The patient says their skin reddens painfully with sun exposure · numerous moles by the patient's own estimate · by self-report, immunosuppression, a family history of skin cancer, a personal history of skin cancer, and no prior organ transplant · a skin lesion imaged with a dermatoscope:
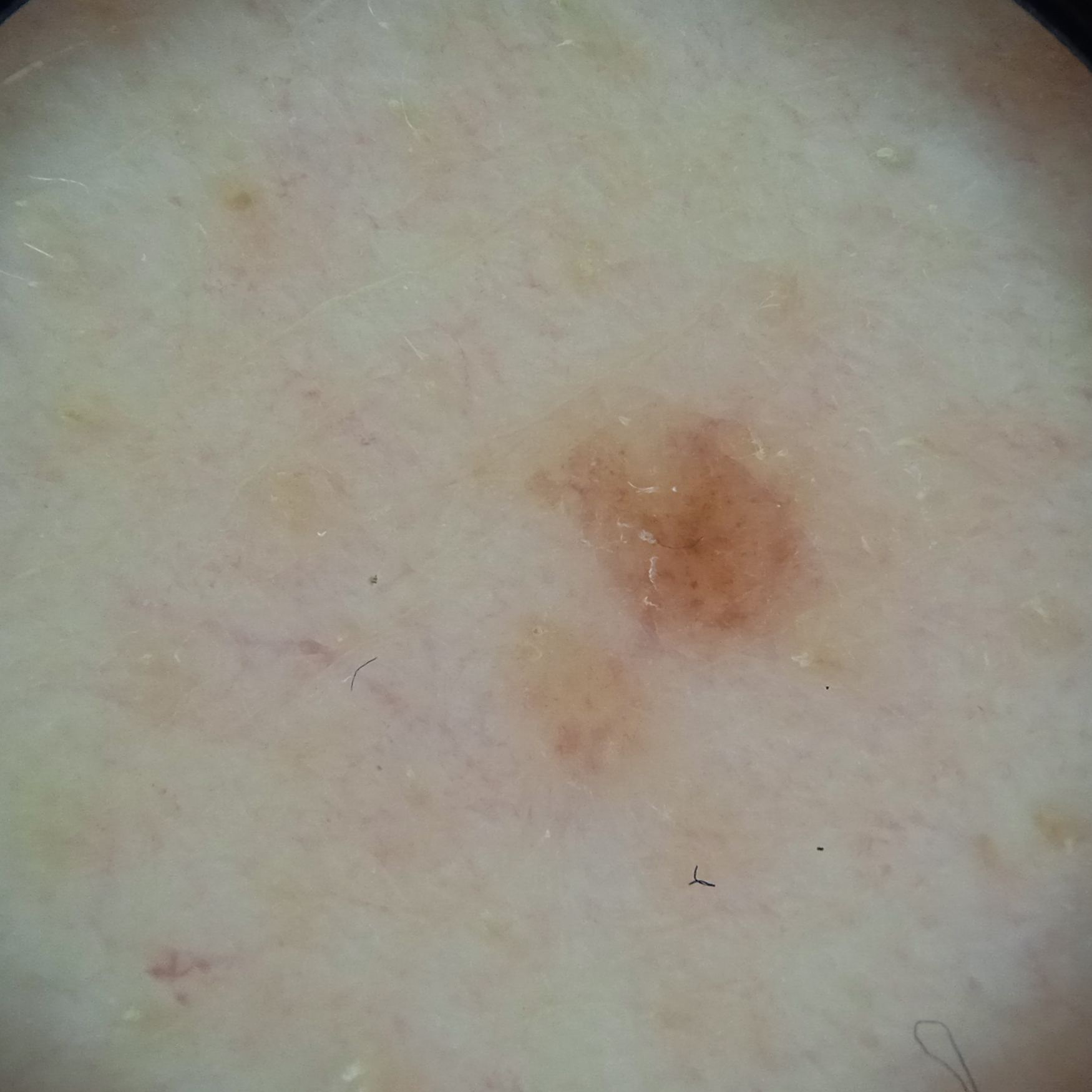  lesion_location: the back
  lesion_size:
    diameter_mm: 2.8
  diagnosis:
    name: melanocytic nevus
    malignancy: benign
    certainty: moderate